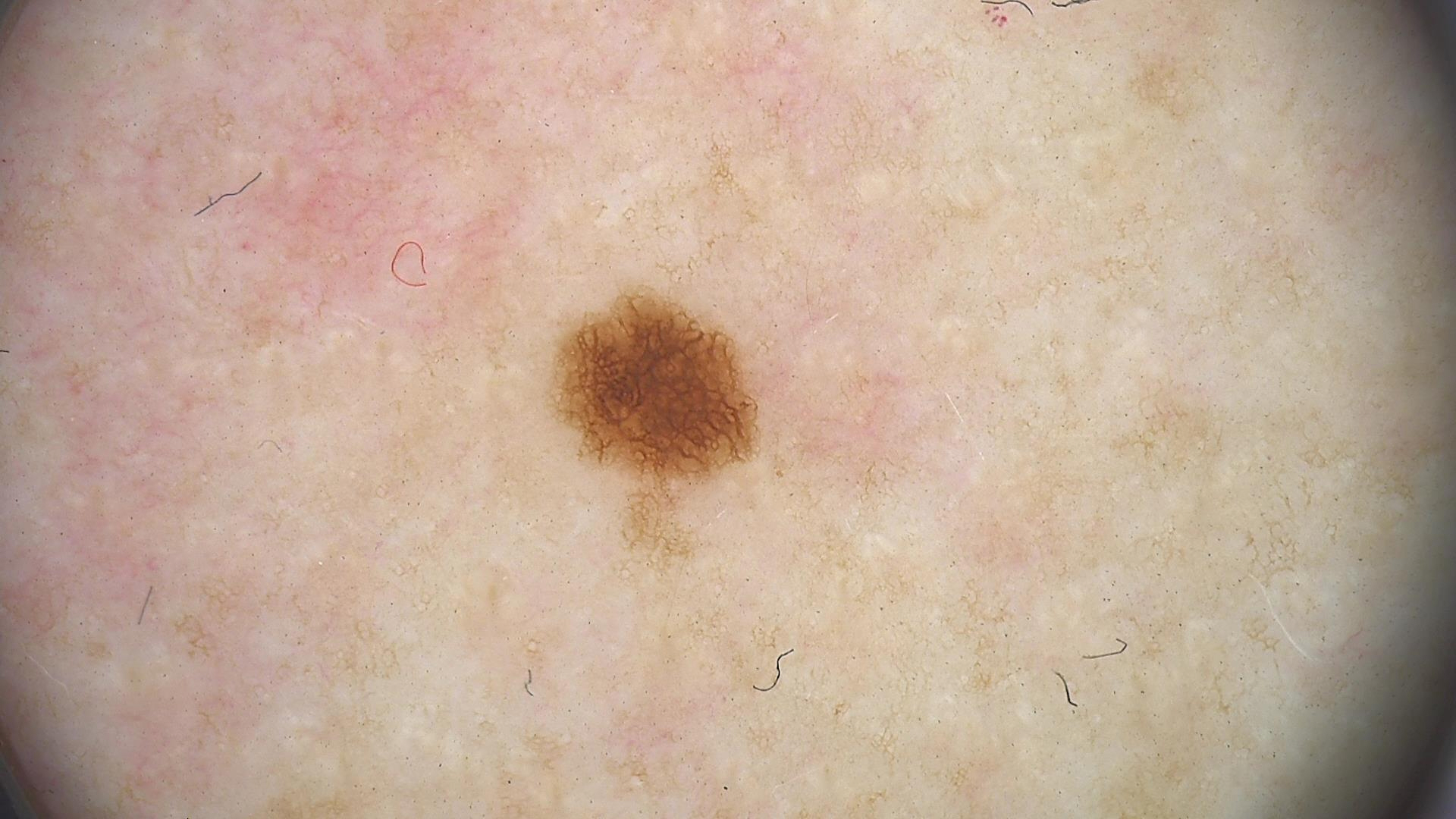image — dermatoscopy; assessment — junctional nevus (expert consensus).